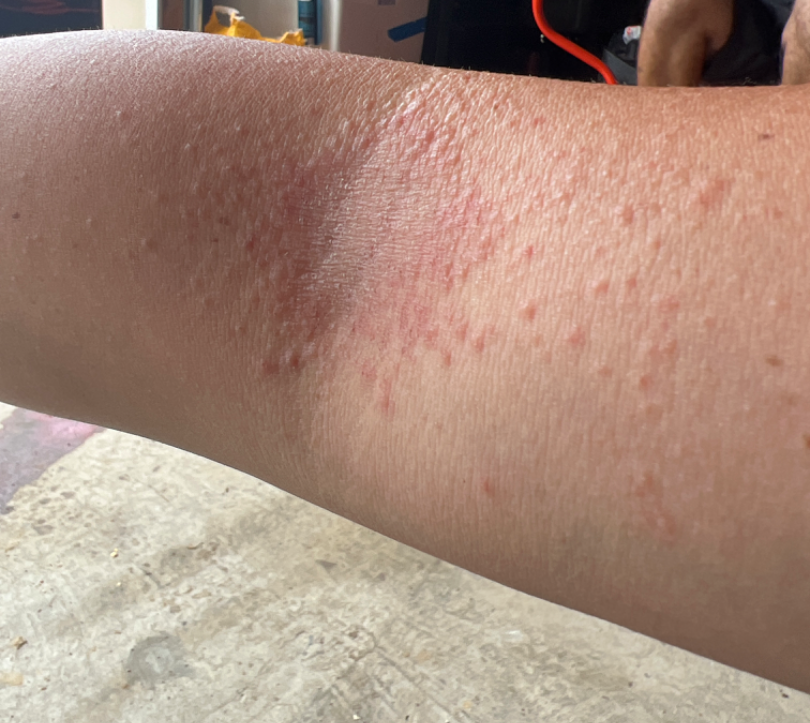view: at an angle | patient: female, age 30–39 | site: arm | diagnostic considerations: favoring Eczema; an alternative is Allergic Contact Dermatitis; lower on the differential is Tinea.